The photograph is a close-up of the affected area, the front of the torso is involved, the subject is a male aged 60–69 — 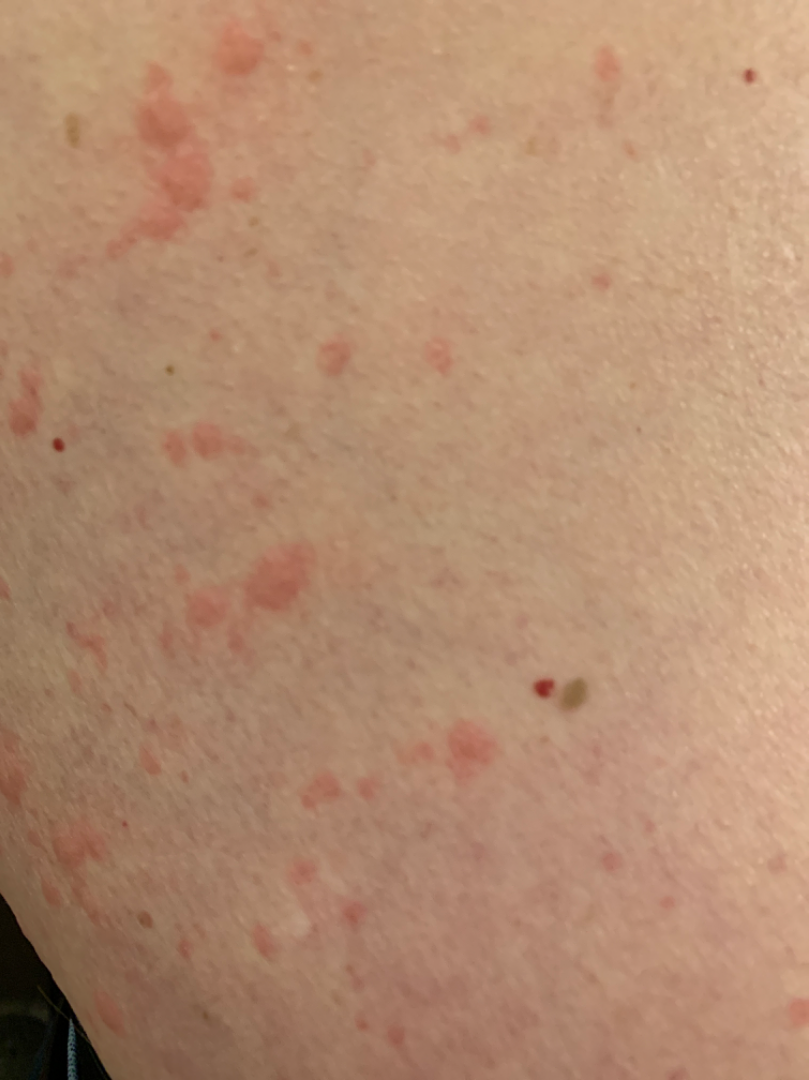Clinical context:
The contributor reports the lesion is rough or flaky. Fitzpatrick II; lay reviewers estimated a Monk skin tone scale of 2. The contributor reports itching. The contributor reports the condition has been present for less than one week. Self-categorized by the patient as a rash.
Assessment:
Most consistent with Urticaria.